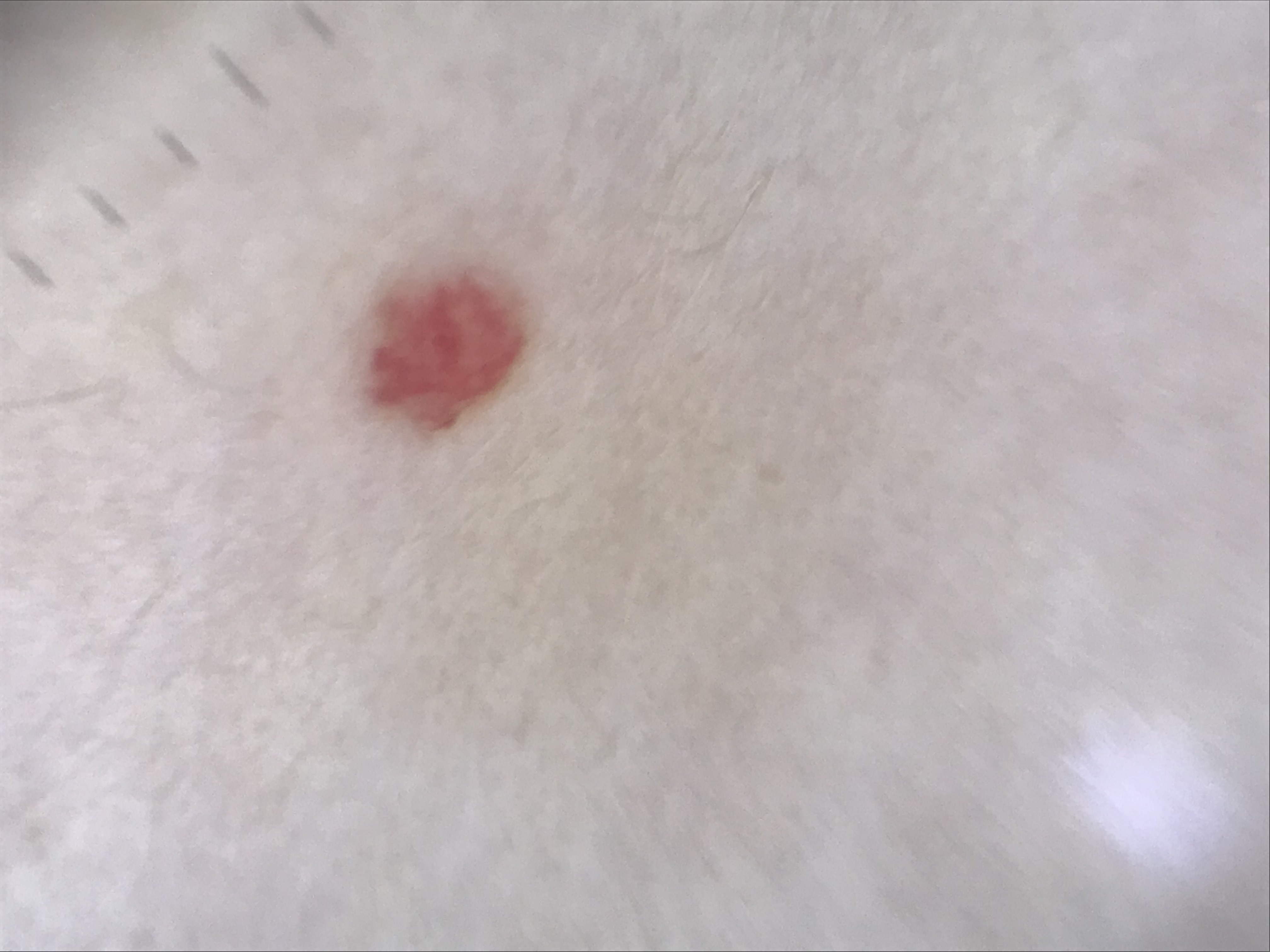Diagnosed as a vascular, benign lesion — a hemangioma.